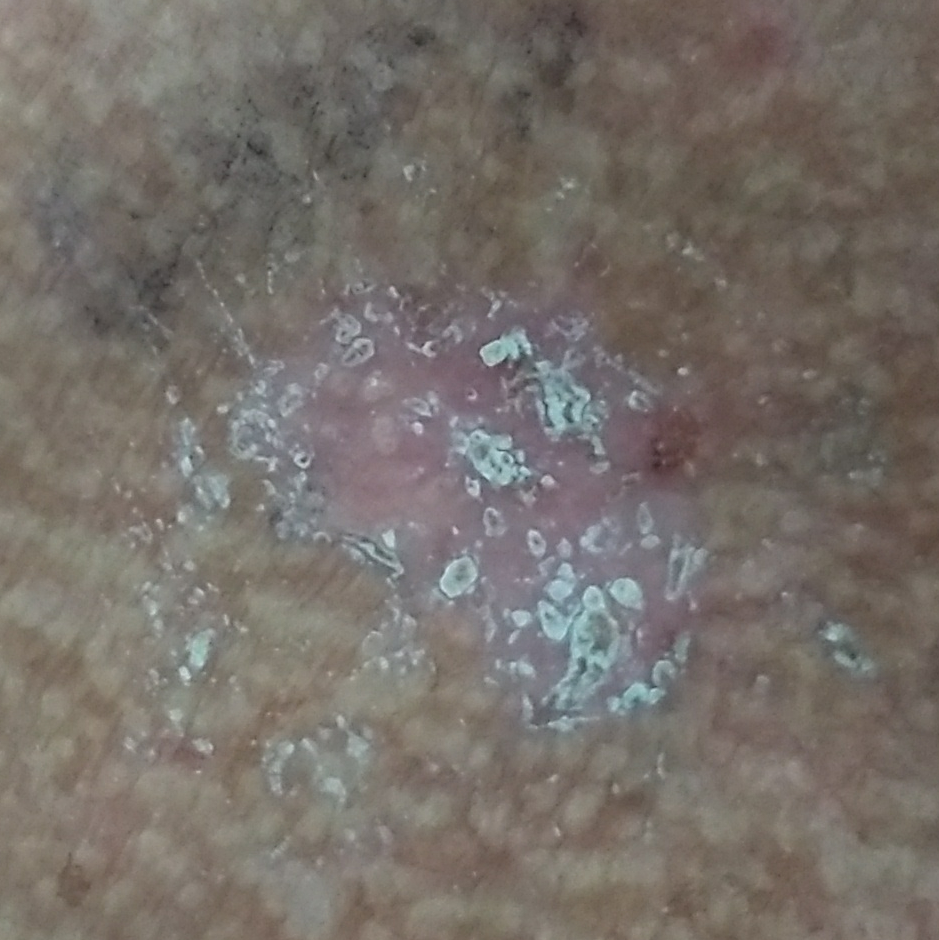Case summary:
The chart notes prior malignancy (patient or family), prior skin cancer (patient or family), and pesticide exposure. A clinical close-up photograph of a skin lesion. A male patient 50 years of age. The patient was assessed as Fitzpatrick II. The lesion measures 35 × 27 mm.
Conclusion:
The biopsy diagnosis was a basal cell carcinoma.